Close-up view — 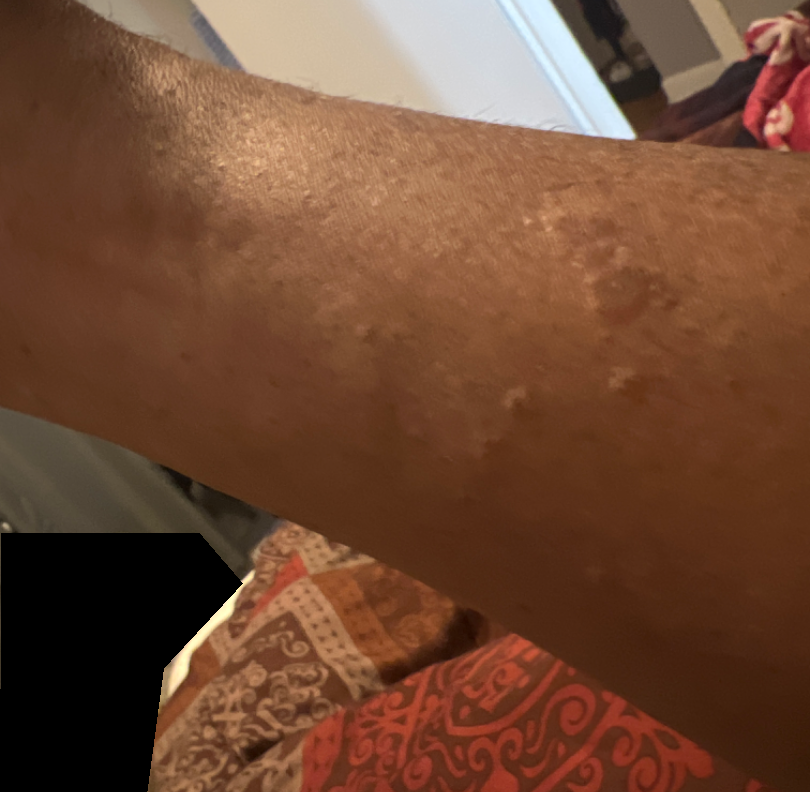The case was indeterminate on photographic review.
The condition has been present for one to four weeks.
The lesion is described as raised or bumpy.